By history, prior malignancy (patient or family) and prior skin cancer (patient or family); the patient is skin type II; a female subject 49 years old; a clinical close-up photograph of a skin lesion:
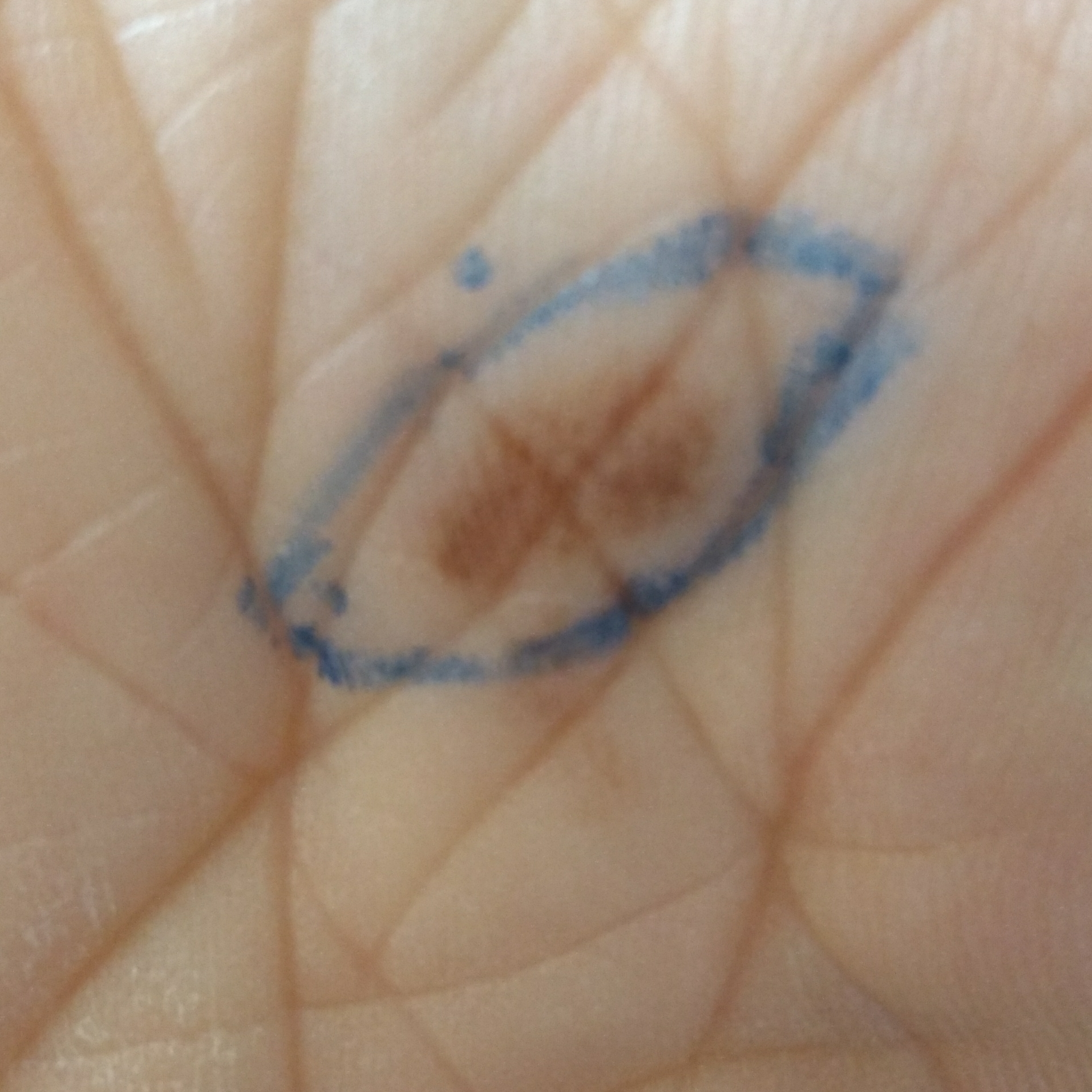Findings:
The lesion involves a foot. The lesion measures 8 × 4 mm. By the patient's account, the lesion does not itch.
Conclusion:
On biopsy, the diagnosis was a benign skin lesion — a nevus.